Close-up view; the lesion involves the arm; the subject is 18–29, female — 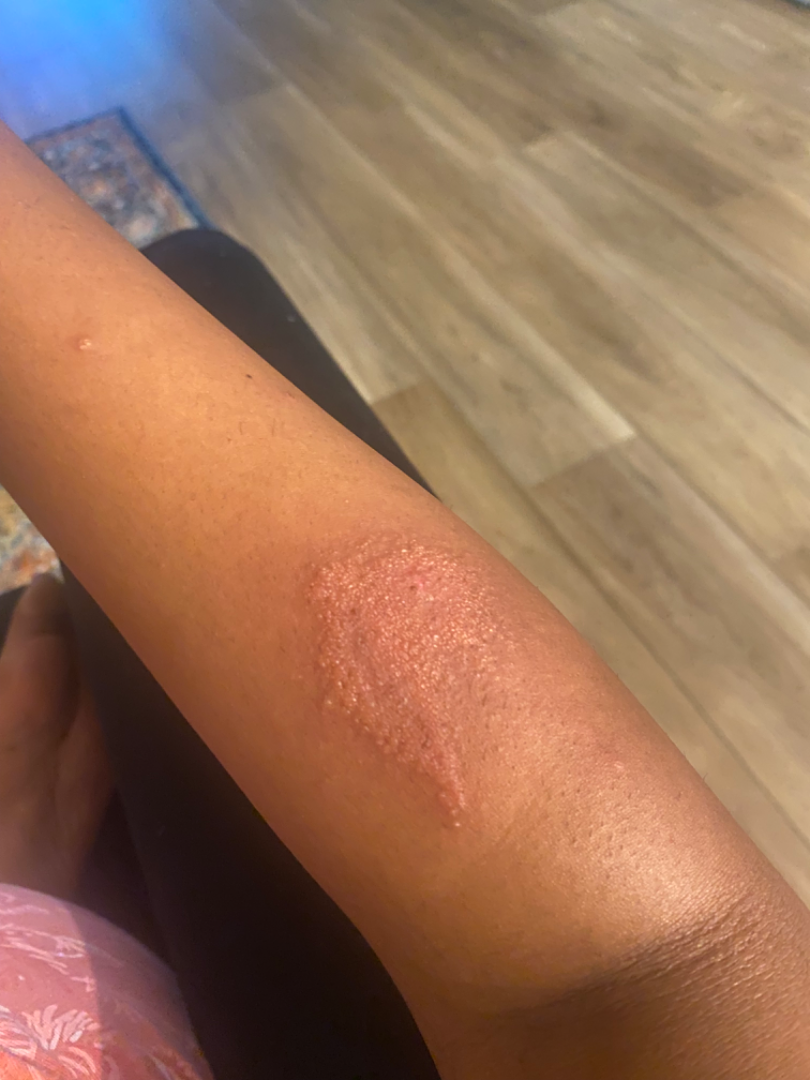clinical impression: the differential includes Impetigo, Psoriasis and Eczema, with no clear leading consideration.